The lesion is described as fluid-filled and raised or bumpy. The arm is involved. Self-categorized by the patient as a rash. Skin tone: Fitzpatrick skin type IV. The contributor reports the condition has been present for about one day. The lesion is associated with bothersome appearance, itching and burning. The photograph was taken at an angle: 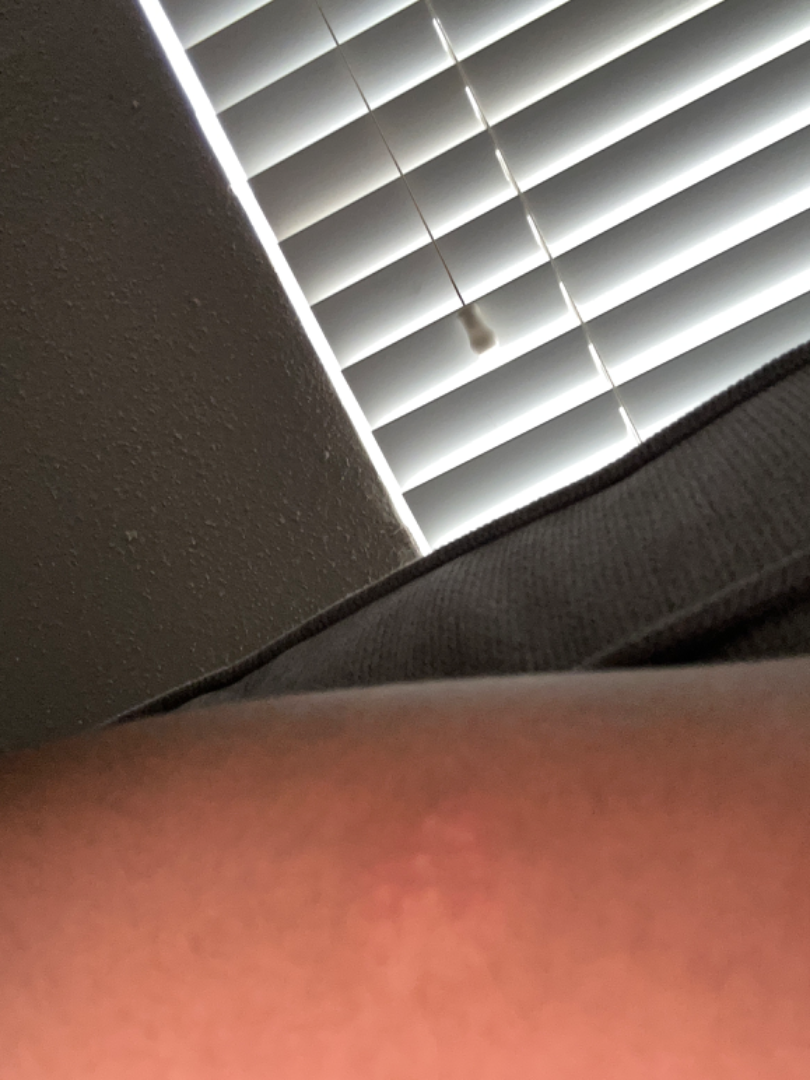Notes:
• clinical impression — Eczema (most likely)